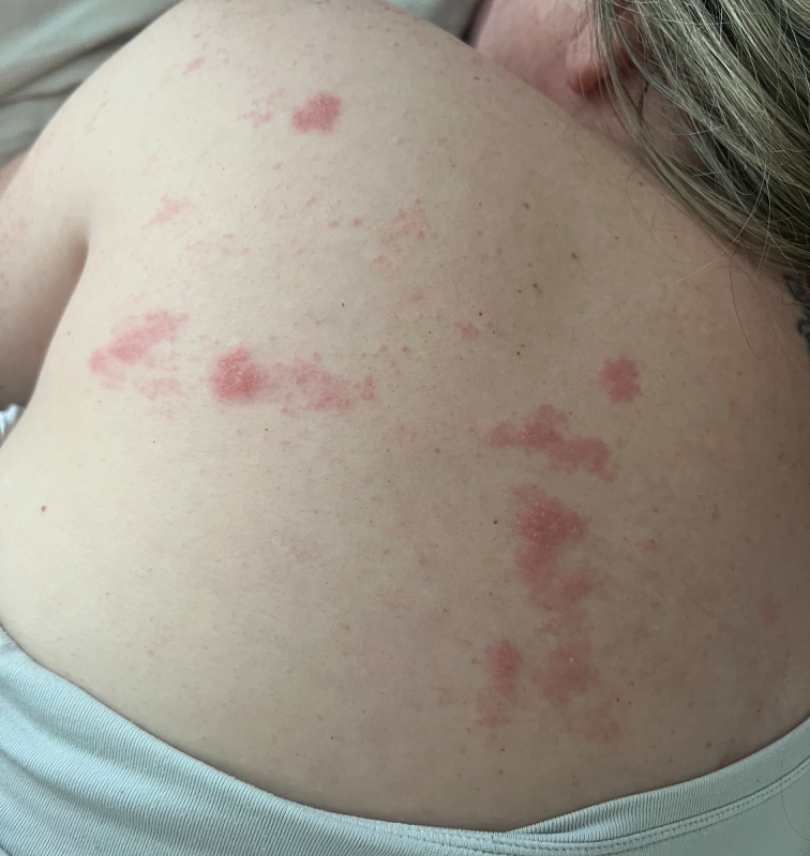{
  "assessment": "indeterminate",
  "patient": "female, age 40–49",
  "shot_type": "close-up"
}